Dermoscopy of a skin lesion, a female patient roughly 20 years of age:
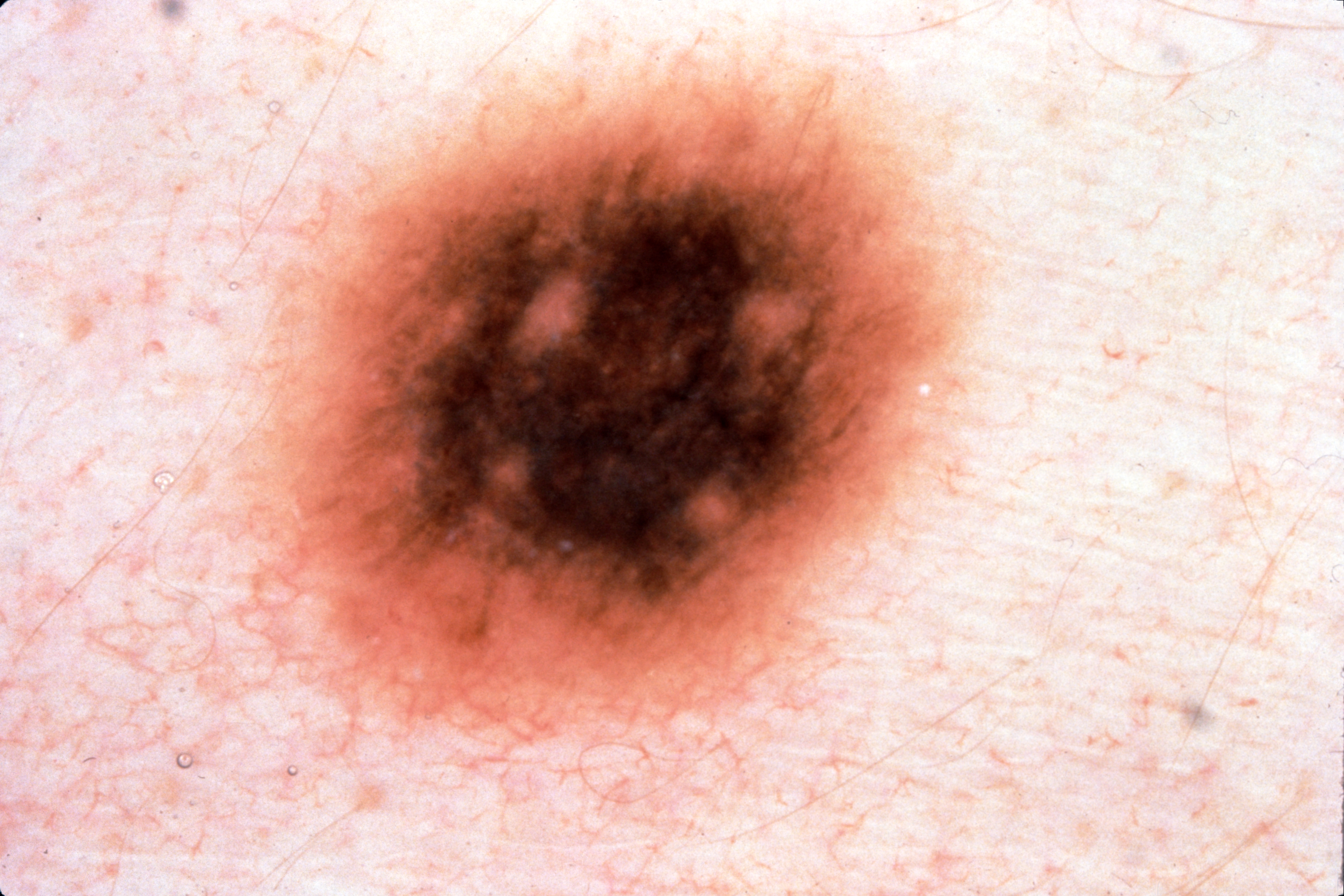lesion bbox: 252/70/966/735 | dermoscopic features assessed but absent: streaks, milia-like cysts, negative network, and pigment network | size: ~30% of the field | assessment: a melanocytic nevus.